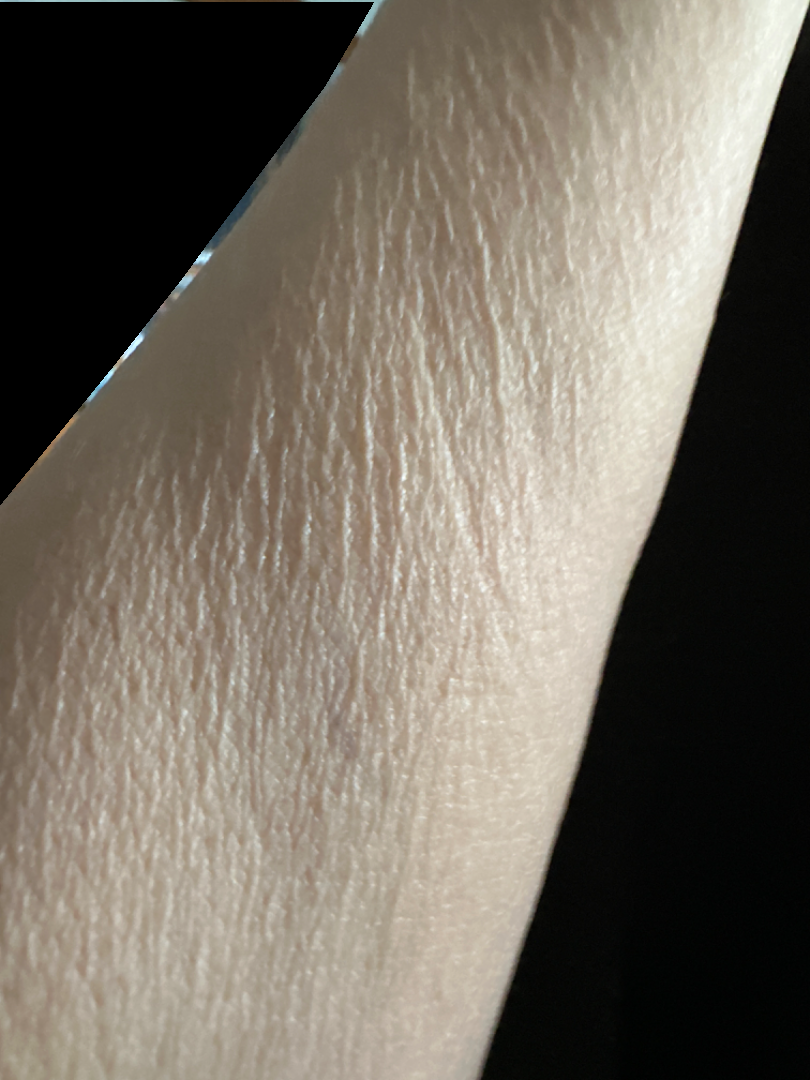image framing: close-up
impression: most consistent with Xerosis